This is a close-up image; the lesion is described as raised or bumpy; female subject, age 30–39; the lesion is associated with itching; reported duration is about one day; the affected area is the leg — 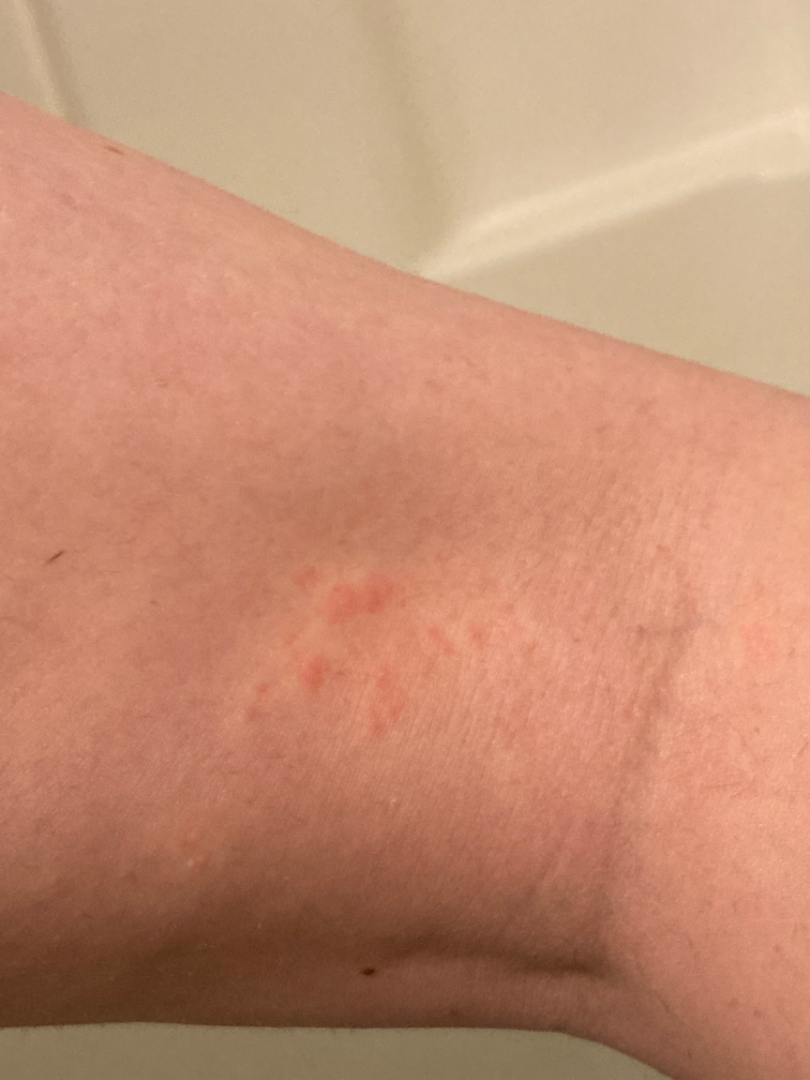On remote review of the image: the leading consideration is Hypersensitivity.